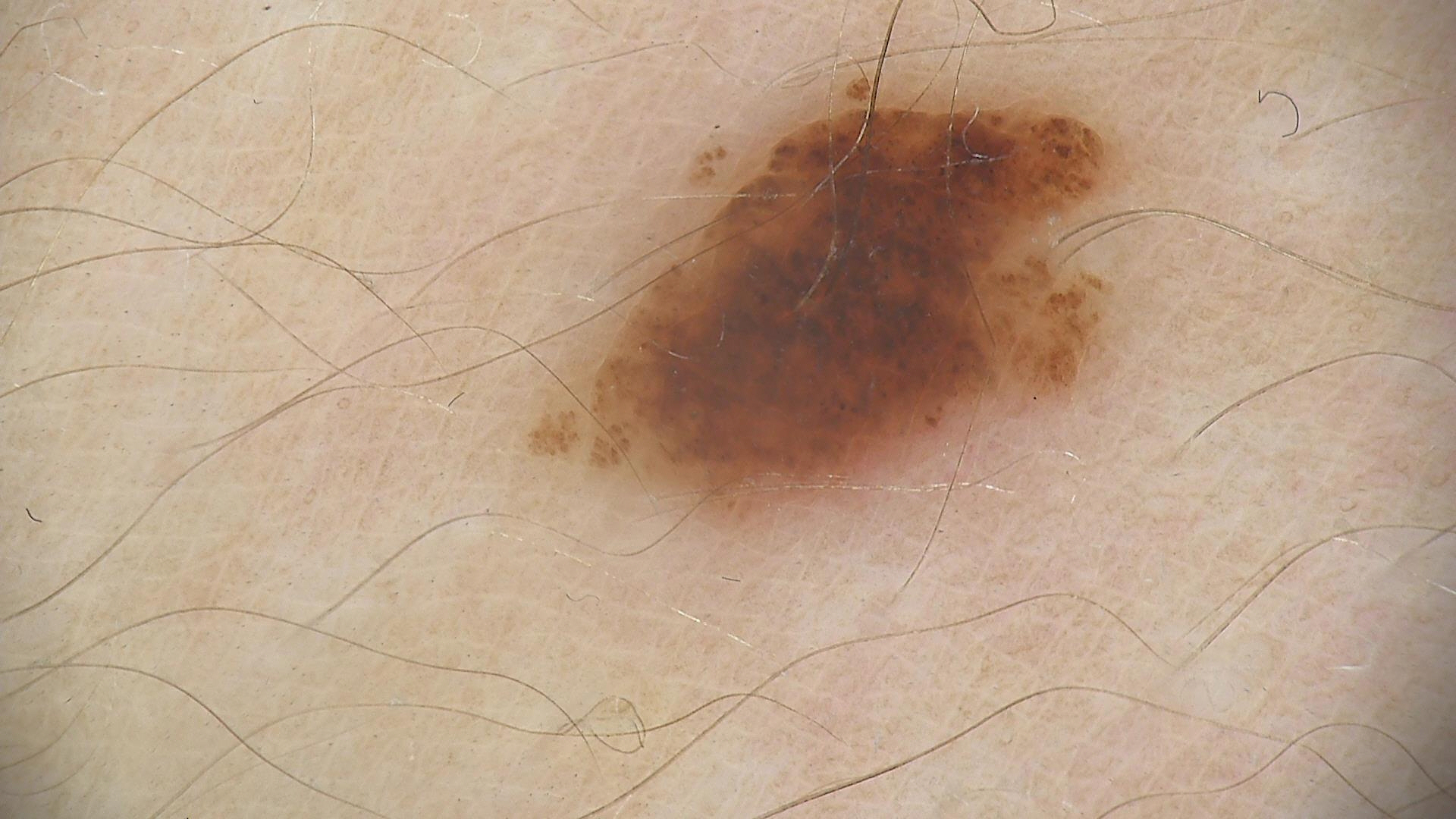* imaging · dermoscopy
* lesion type · banal
* class · compound nevus (expert consensus)